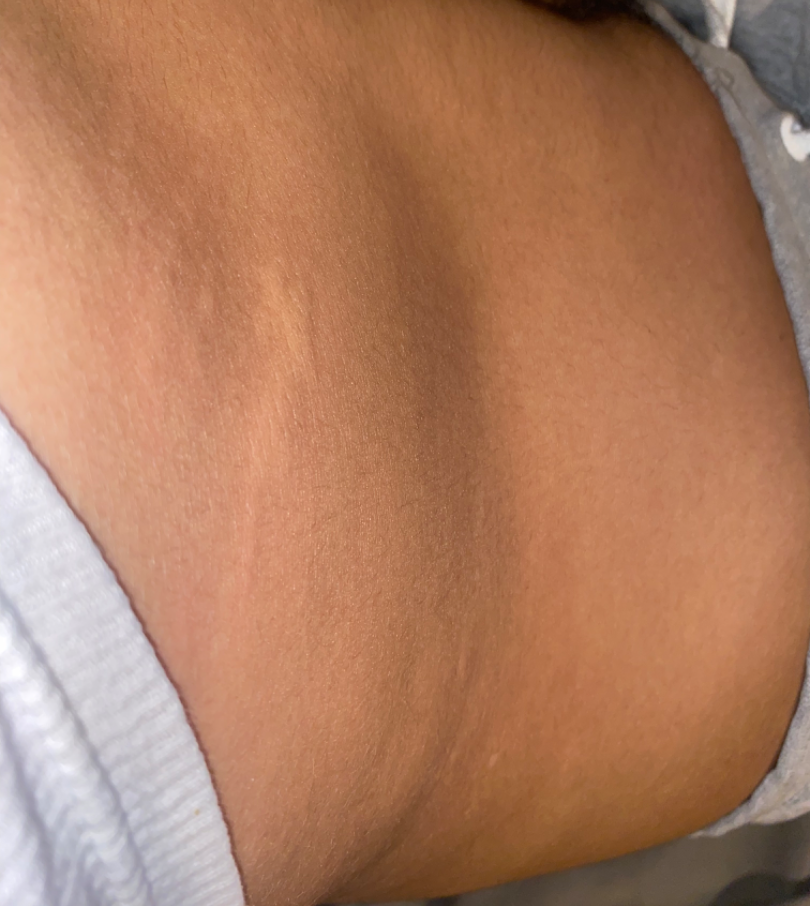{"body_site": "front of the torso", "patient": "male", "shot_type": "close-up", "differential": {"leading": ["Urticaria"], "considered": ["Allergic Contact Dermatitis"], "unlikely": ["Insect Bite"]}}